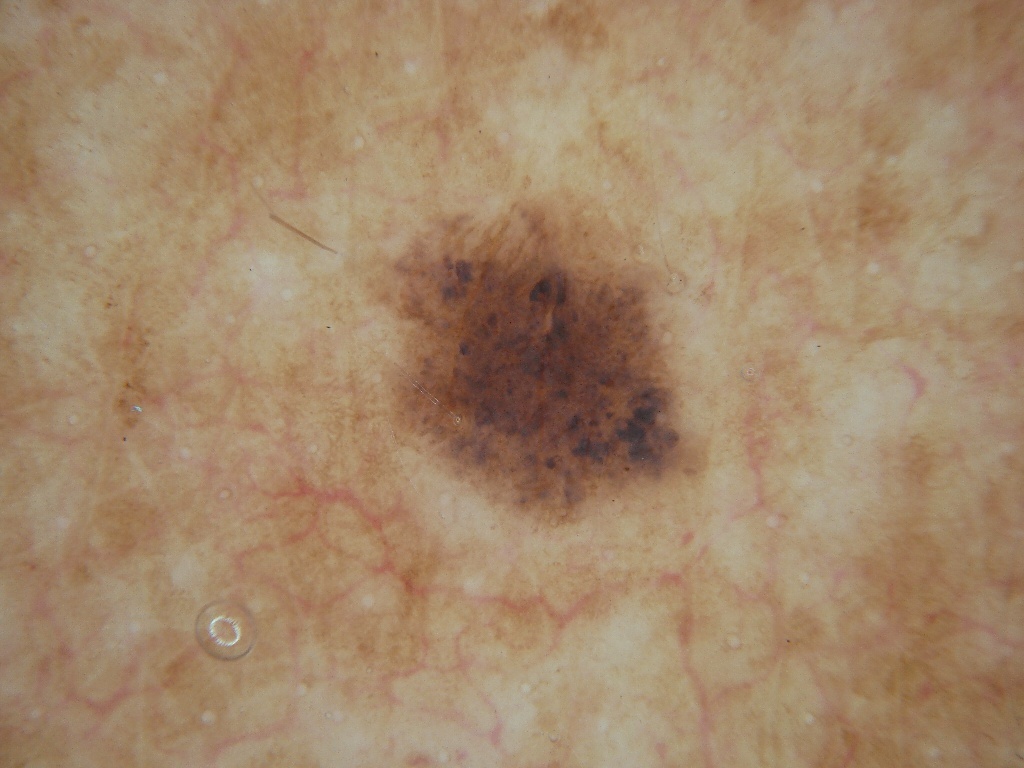{
  "image": {
    "modality": "dermoscopy"
  },
  "lesion_location": {
    "bbox_xyxy": [
      344,
      176,
      721,
      552
    ]
  },
  "diagnosis": {
    "name": "melanocytic nevus",
    "malignancy": "benign",
    "lineage": "melanocytic",
    "provenance": "clinical"
  }
}